Acquired for a research image collection, with no referral diagnosis. A dermatoscopic image of a skin lesion. A male patient 78 years old.
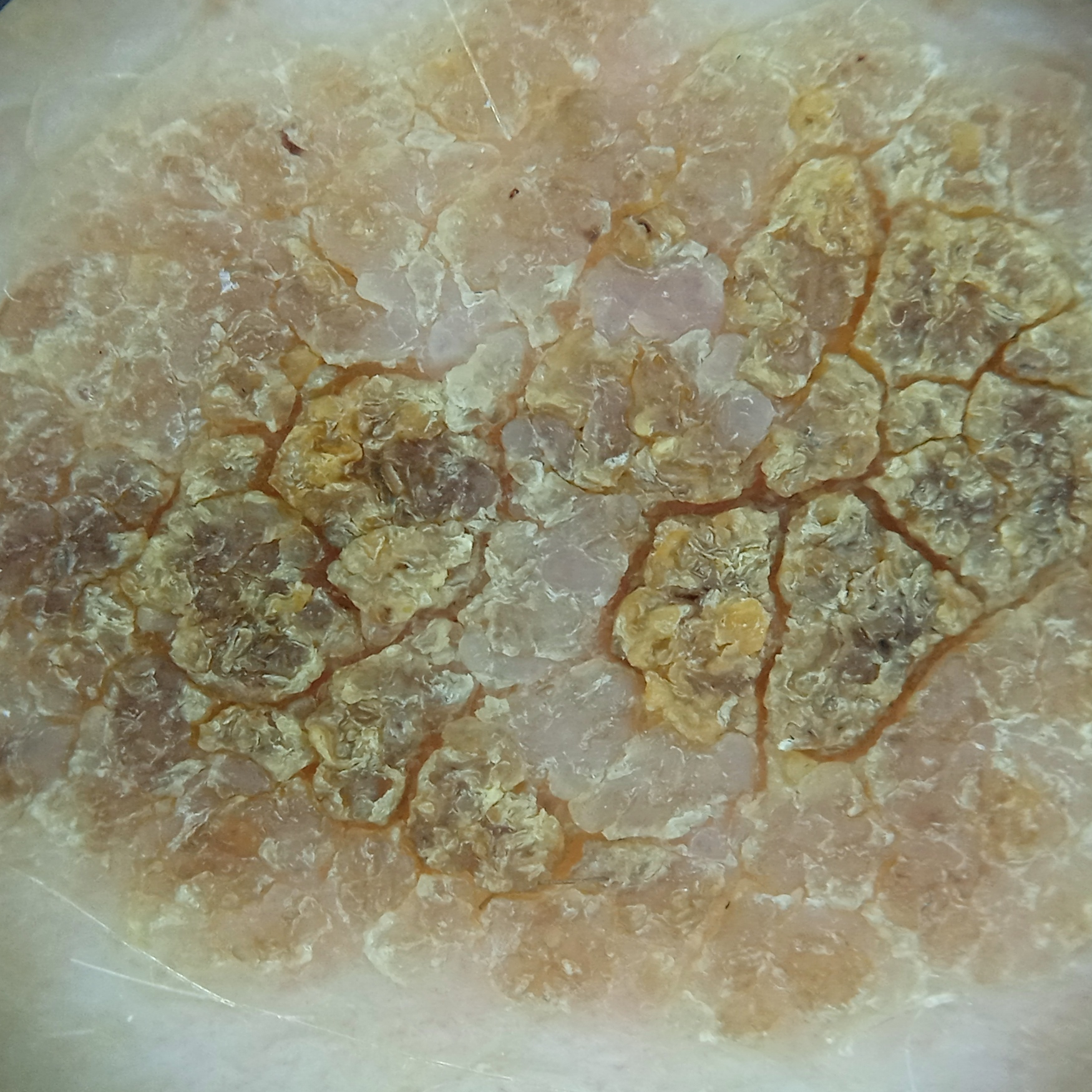– body site — the back
– lesion size — 15.1 mm
– diagnostic label — seborrheic keratosis (dermatologist consensus)